This is a close-up image.
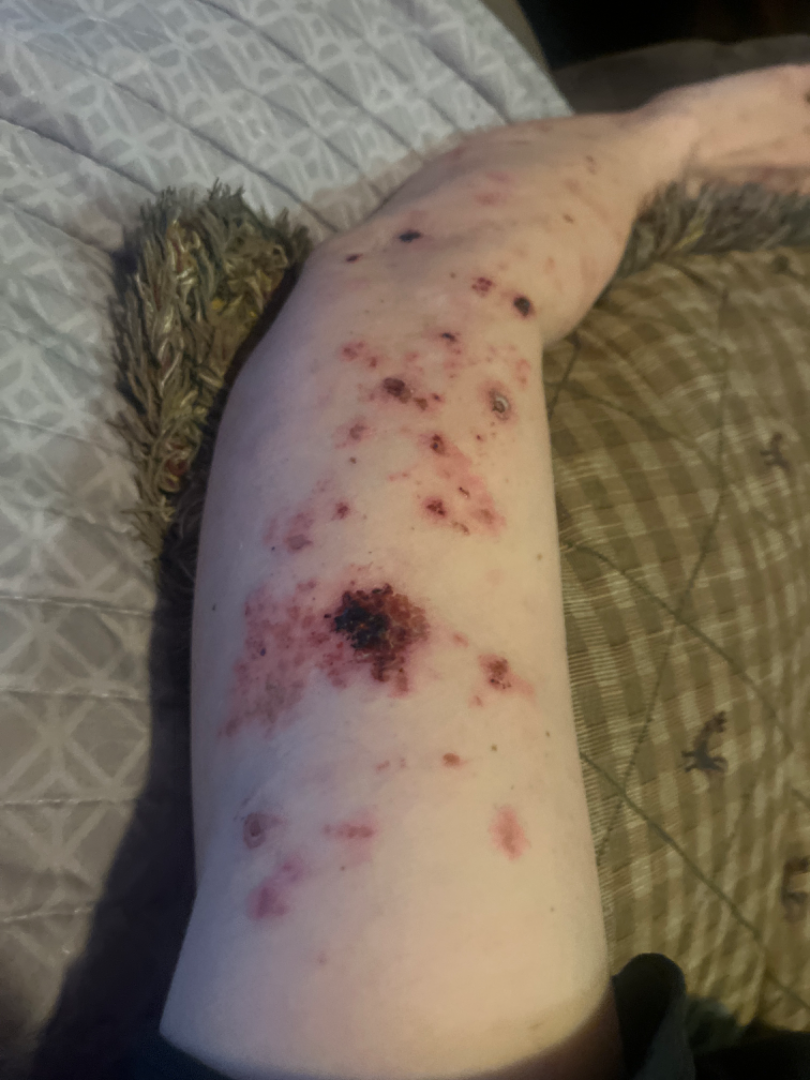Impression:
On remote dermatologist review: Infected eczema, Herpes Zoster and Leukocytoclastic Vasculitis were each considered, in no particular order.